The leg is involved · the photo was captured at a distance: 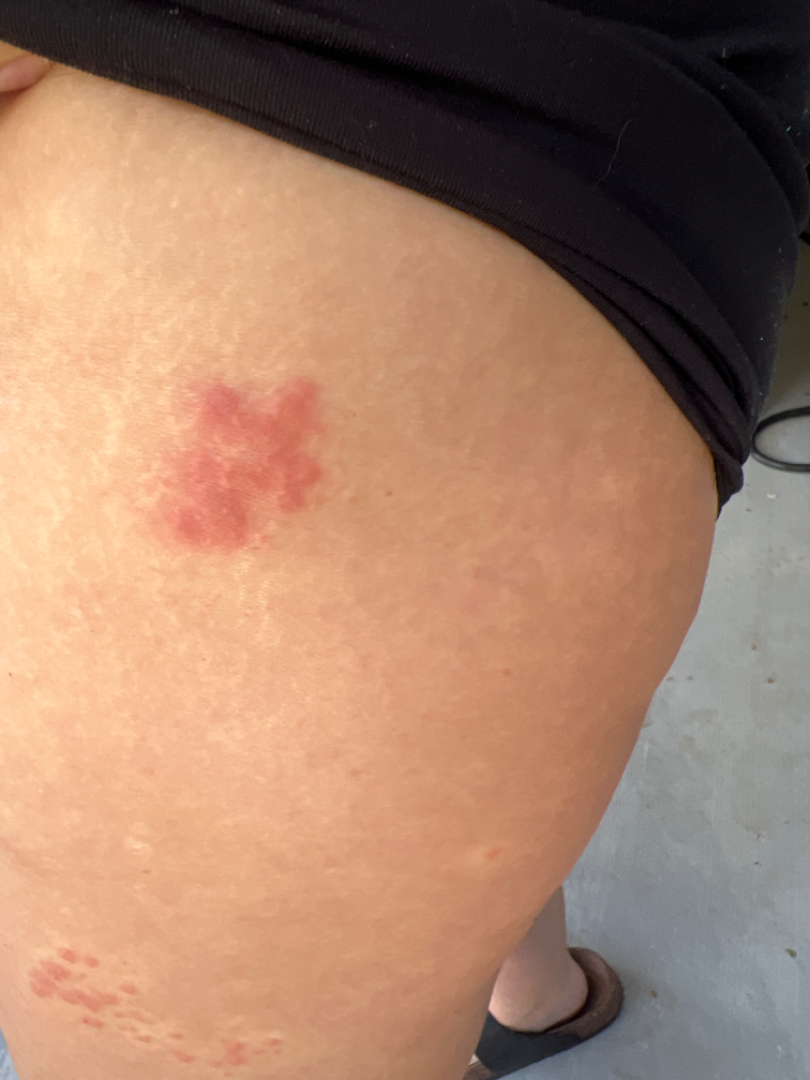Diagnostic features were not clearly distinguishable in this photograph.